Located on the leg · the patient is 30–39, male · the photo was captured at an angle · self-categorized by the patient as a rash · skin tone: Fitzpatrick II; lay reviewers estimated Monk Skin Tone 3 (US pool) or 4 (India pool) · the contributor reports the lesion is rough or flaky · symptoms reported: itching, bothersome appearance and darkening: 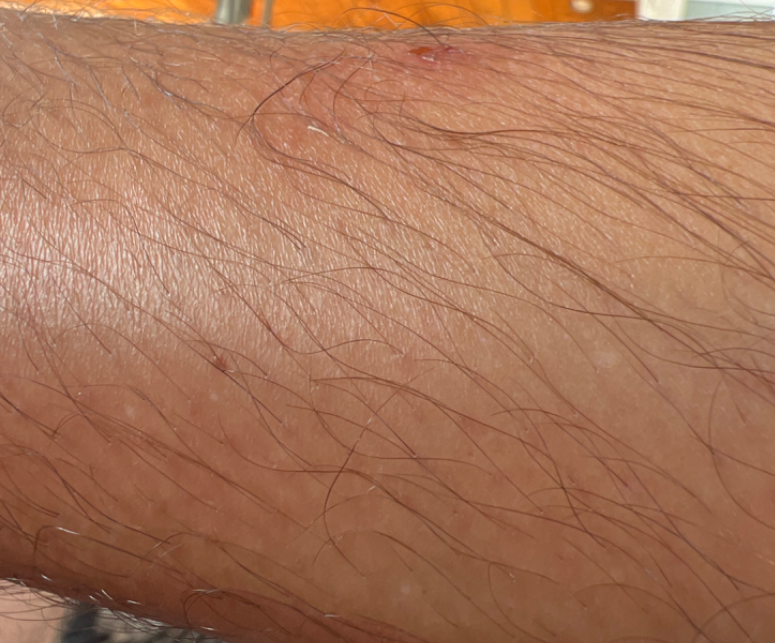clinical impression — most likely Insect Bite; also consider Allergic Contact Dermatitis; a remote consideration is Localized skin infection; less likely is Infected eczema